Reported lesion symptoms include bothersome appearance, enlargement and itching; this image was taken at an angle; the contributor reports the lesion is rough or flaky and raised or bumpy; female patient, age 50–59; Fitzpatrick phototype III; the lesion involves the front of the torso and back of the torso; self-categorized by the patient as skin that appeared healthy to them; the condition has been present for less than one week.
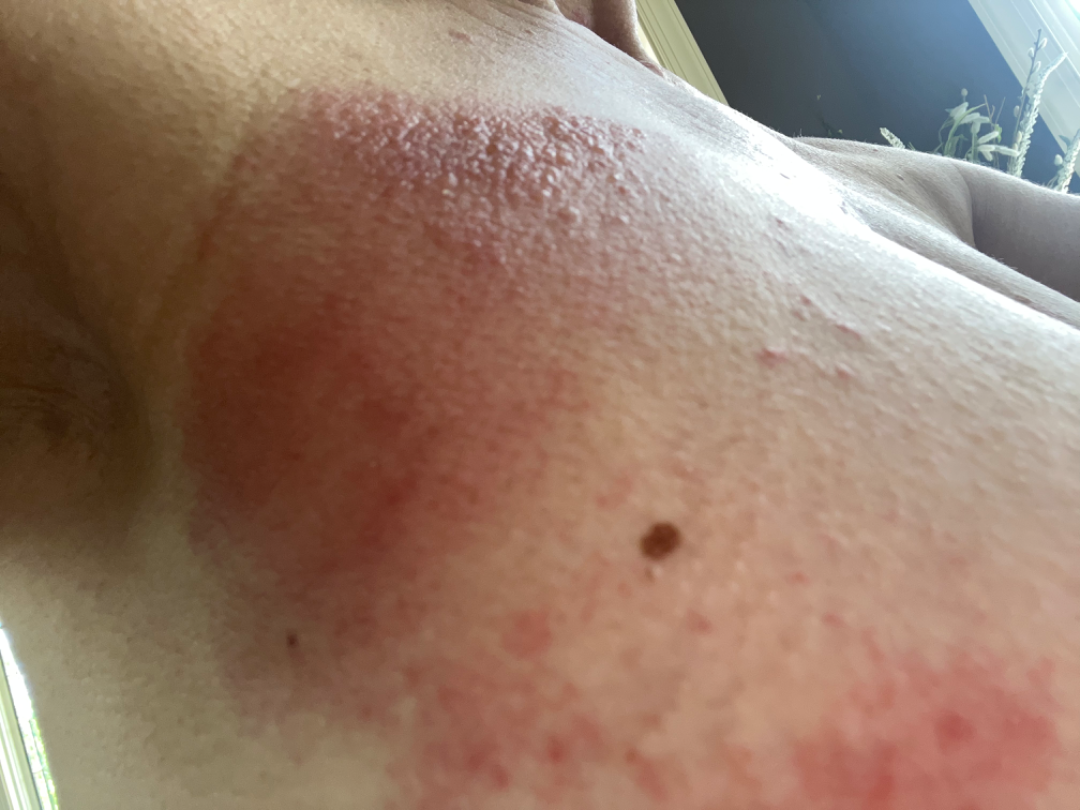Notes:
* assessment · indeterminate